The contributor reports the lesion is raised or bumpy and flat · close-up view · self-categorized by the patient as a rash · FST IV; non-clinician graders estimated a Monk Skin Tone of 5 · female subject, age 18–29 · the patient reported no relevant symptoms from the lesion · reported duration is about one day.
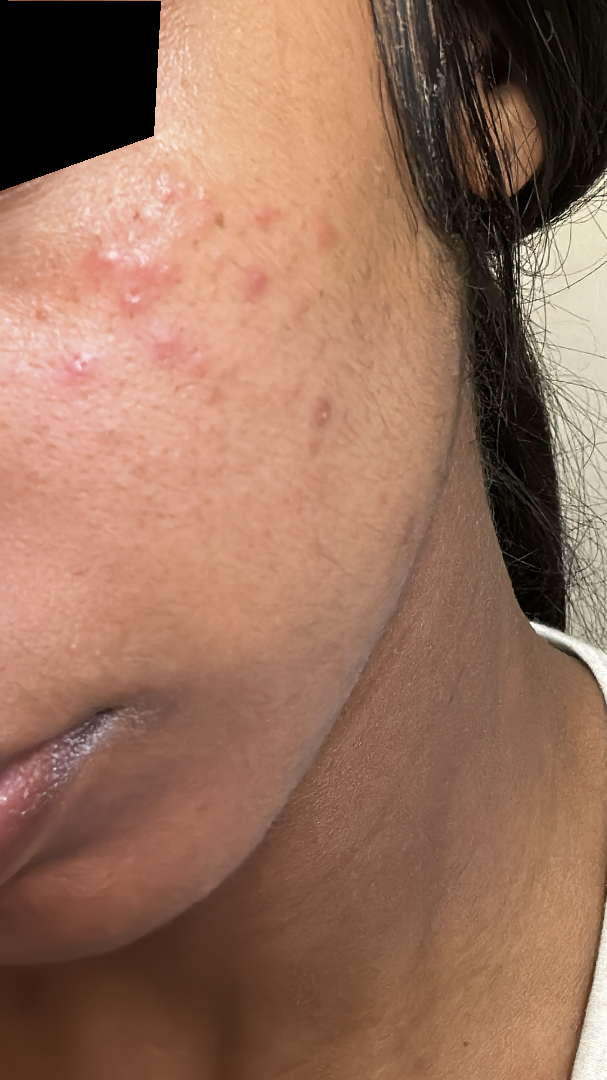Case summary:
* diagnostic considerations · Acne (considered); Rosacea (considered)